A dermoscopic photograph of a skin lesion.
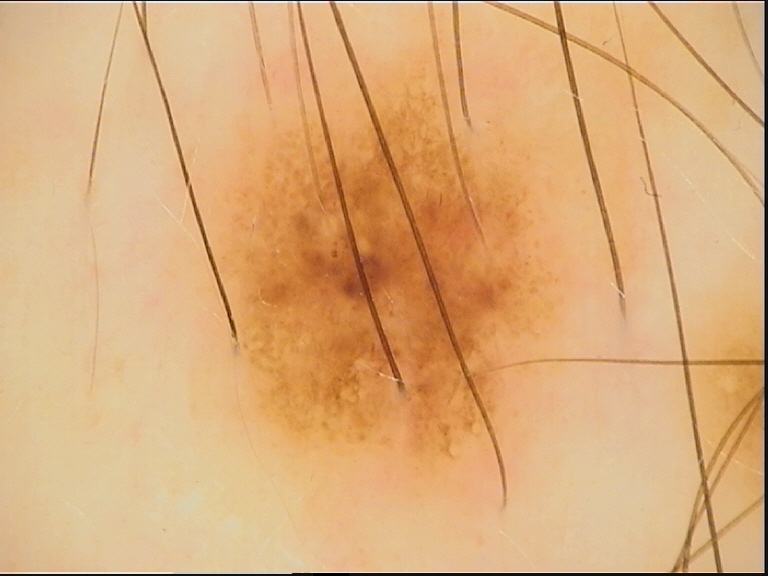Findings:
- label · dysplastic junctional nevus (expert consensus)